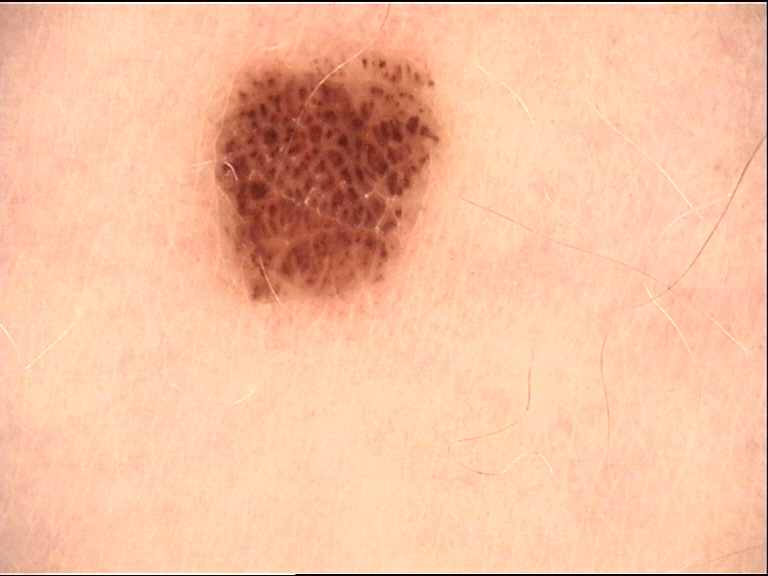Findings: The morphology is that of a banal lesion. Impression: The diagnosis was a compound nevus.